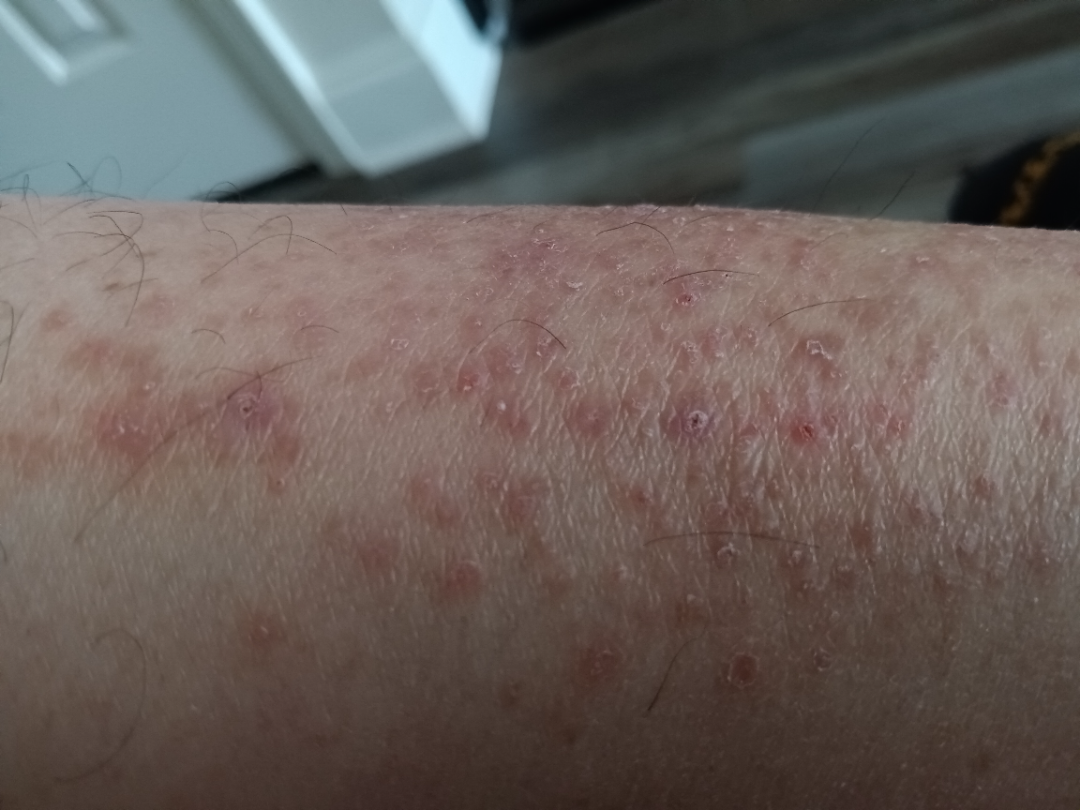The photograph was taken at an angle. The lesion is described as raised or bumpy. The lesion is associated with itching and bothersome appearance. The contributor is male. No constitutional symptoms were reported. The contributor reports the condition has been present for three to twelve months. The affected area is the leg. Self-categorized by the patient as a rash. On photographic review, Eczema (most likely); Acute and chronic dermatitis (possible); Allergic Contact Dermatitis (unlikely); Pigmented purpuric eruption (unlikely); Drug Rash (unlikely).